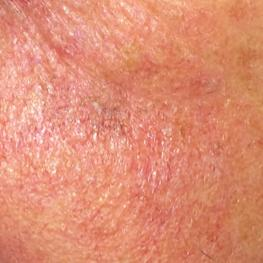Findings:
– body site — the face
– symptoms — itching
– diagnosis — actinic keratosis (clinical consensus)